The subject is female, the arm is involved, this is a close-up image — 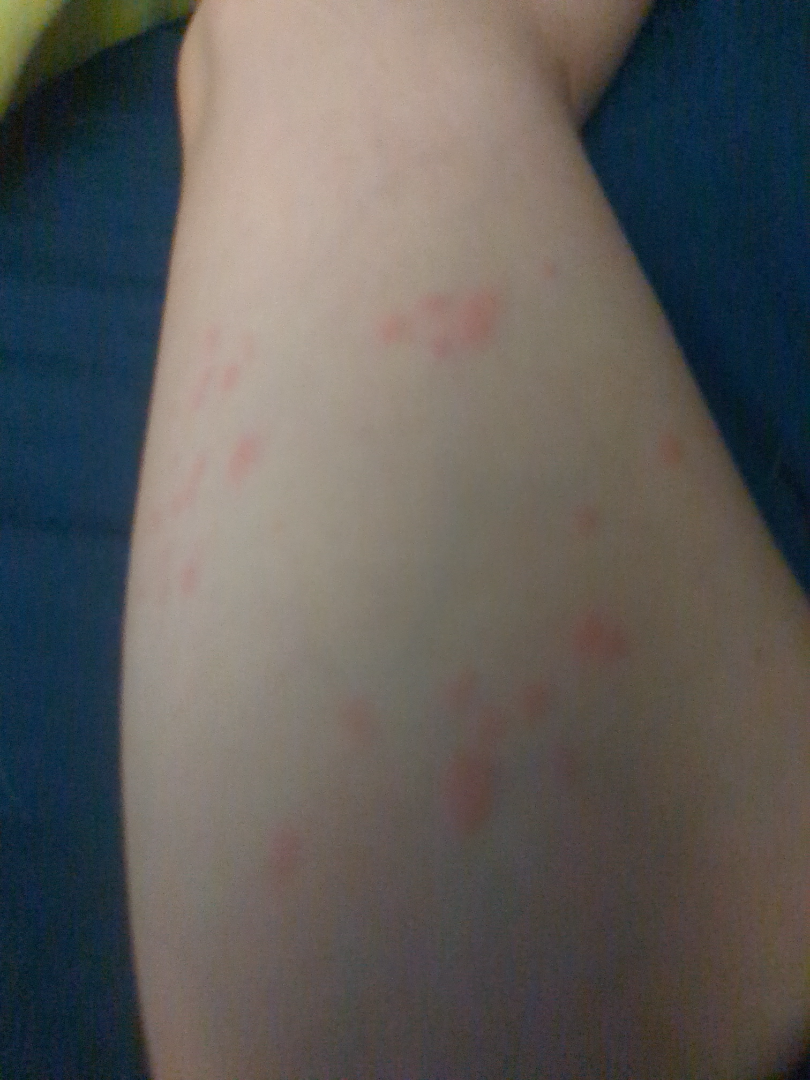Assessment: The skin condition could not be confidently assessed from this image. Clinical context: The lesion is described as raised or bumpy. Reported lesion symptoms include bothersome appearance. The patient reported no systemic symptoms. The patient considered this a rash. The patient indicates the condition has been present for less than one week.